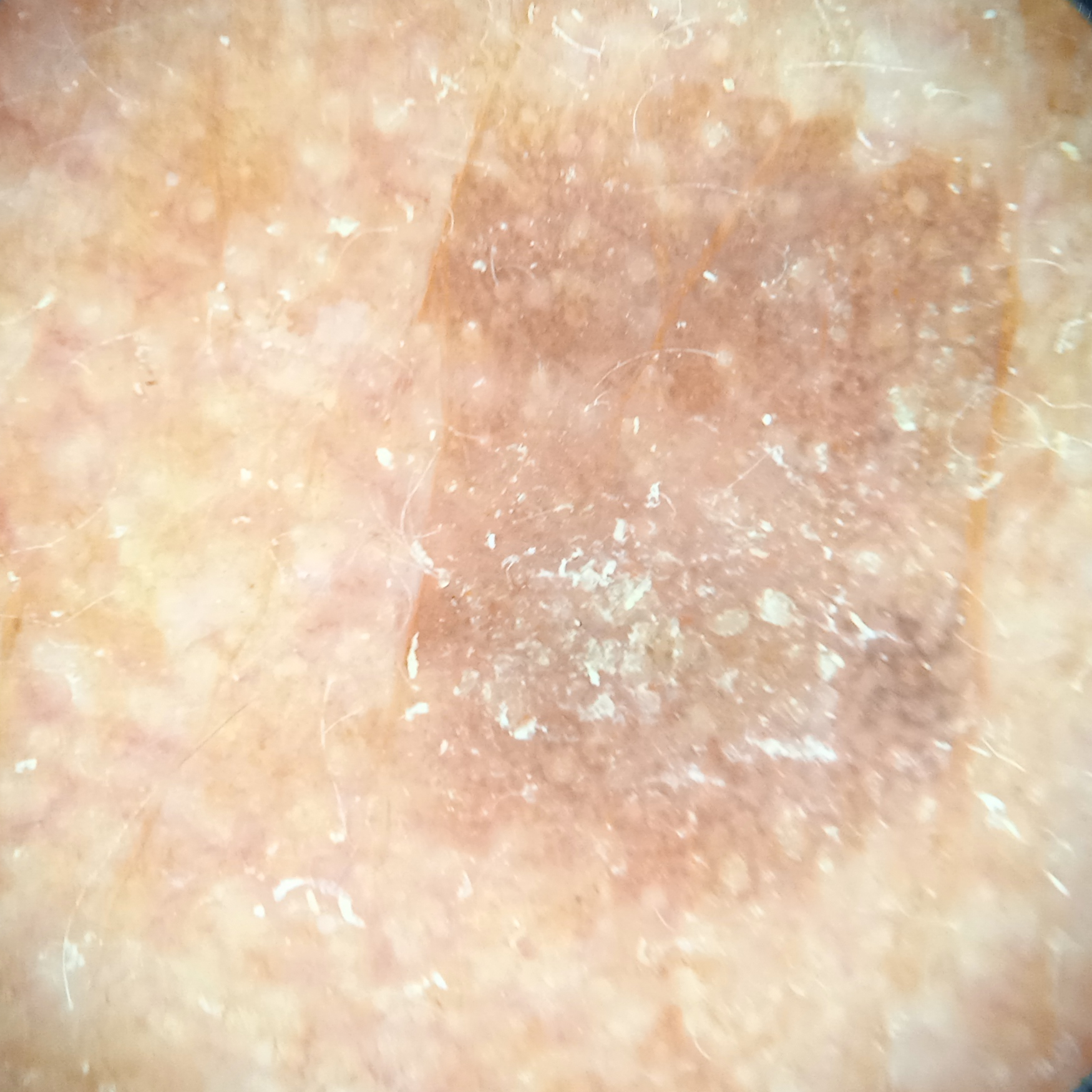patient — male, 76 years old; referral — clinical suspicion of basal cell carcinoma; image type — dermoscopy; nevus count — few melanocytic nevi overall; risk factors — a personal history of skin cancer, a personal history of cancer; sun reaction — skin reddens with sun exposure; site — the face; diameter — 8.7 mm; pathology — basal cell carcinoma (biopsy-proven).